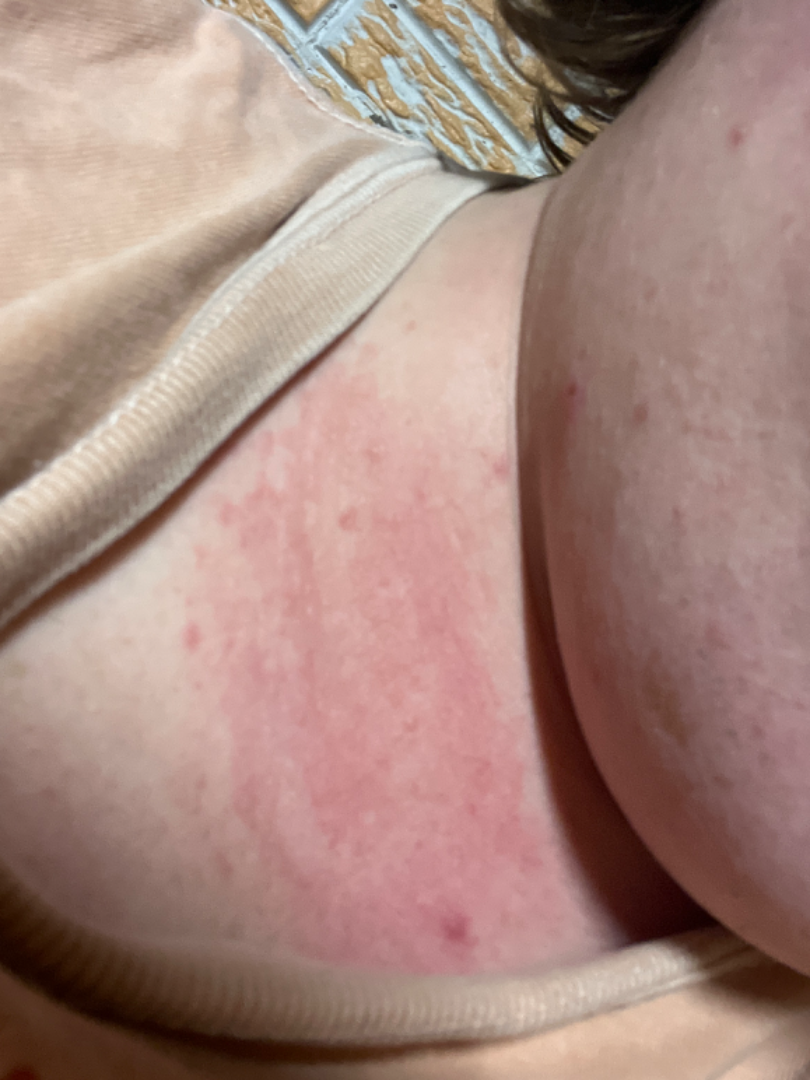Patient information:
Present for one to three months. The photo was captured at an angle. The patient is a female aged 30–39. The head or neck is involved. The patient indicates the lesion is raised or bumpy. Self-categorized by the patient as a rash.
Review:
The differential, in no particular order, includes Allergic Contact Dermatitis and Irritant Contact Dermatitis.